Dermoscopy of a skin lesion.
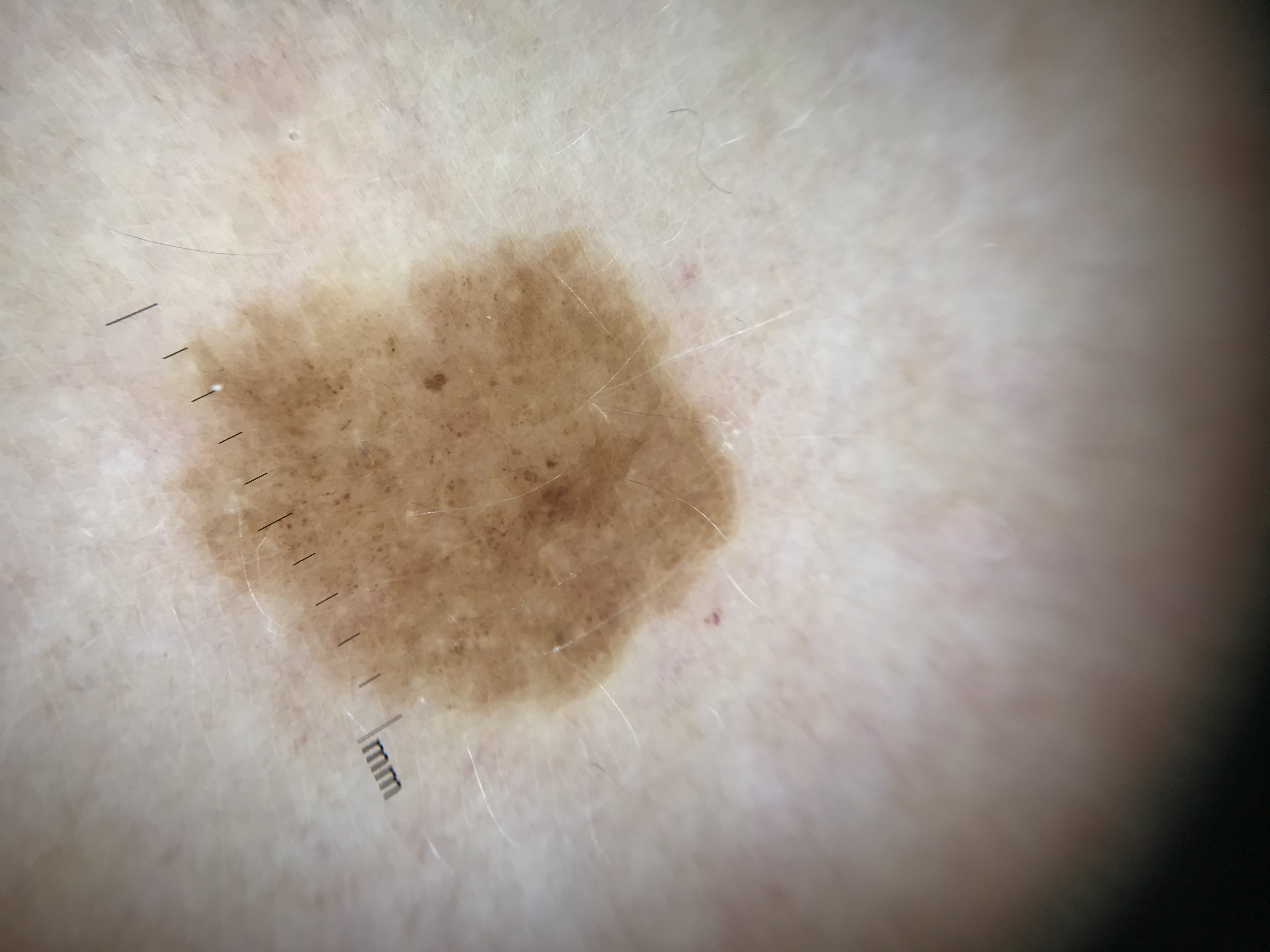diagnosis: dysplastic junctional nevus (expert consensus).